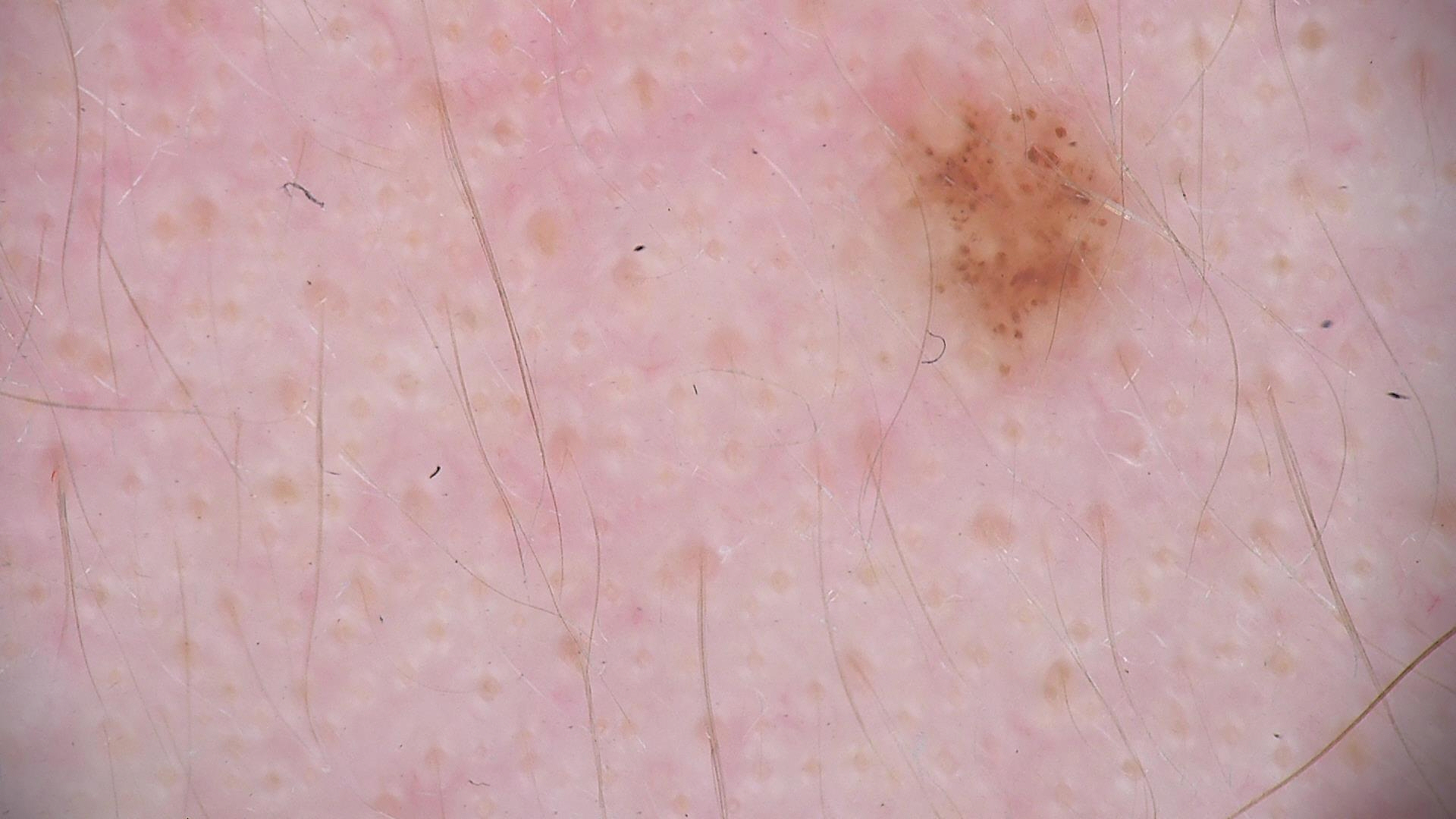A dermoscopic close-up of a skin lesion. Labeled as a dysplastic junctional nevus.